The lesion involves the arm, this image was taken at a distance — 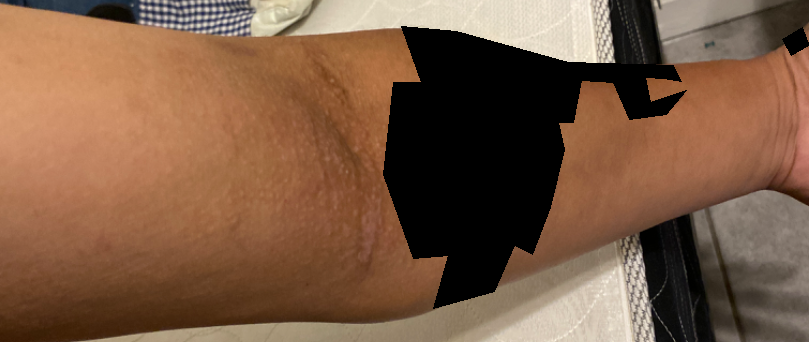Present for one to three months. The patient notes the lesion is rough or flaky. The reviewing clinician's impression was: consistent with Eczema.